A male subject aged 83 or over · a wide-field clinical photograph of a skin lesion — 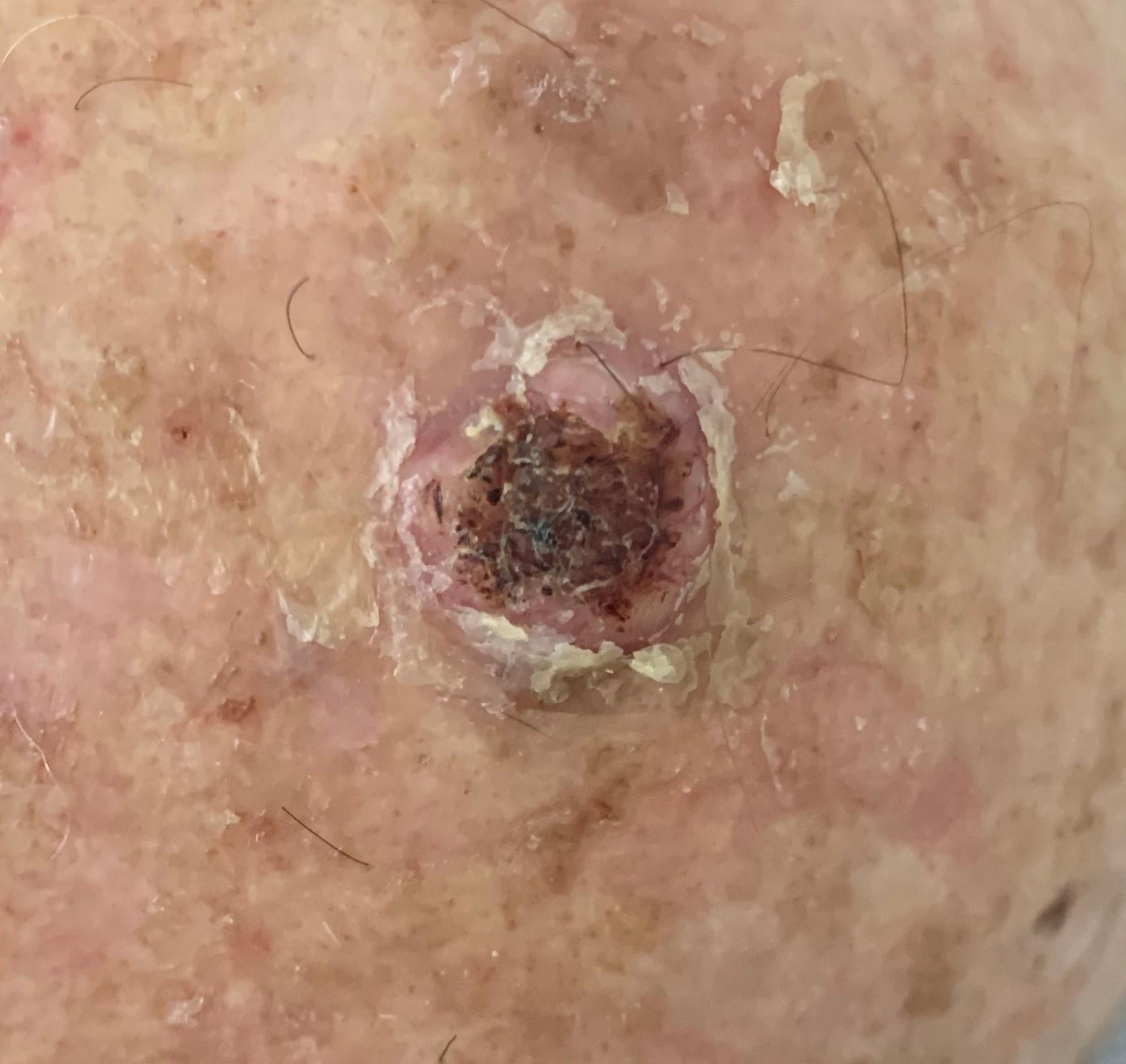Histopathology confirmed an epidermal lesion — a squamous cell carcinoma.